A male subject aged around 60. A skin lesion imaged with a dermatoscope — 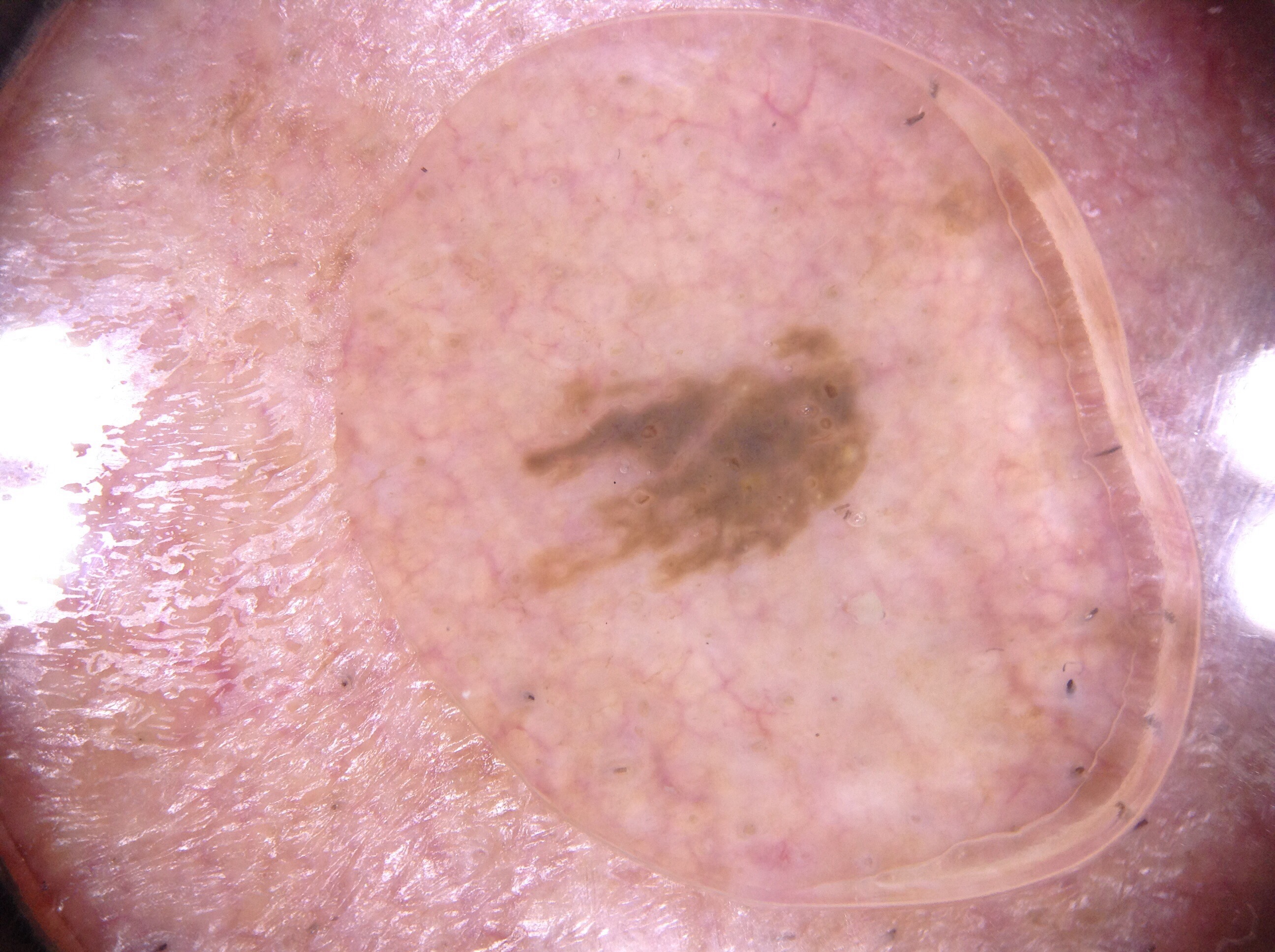dermoscopic_features:
  present:
    - milia-like cysts
  absent:
    - negative network
    - pigment network
    - streaks
lesion_location:
  bbox_xyxy:
    - 492
    - 281
    - 933
    - 619
diagnosis:
  name: seborrheic keratosis
  malignancy: benign
  lineage: keratinocytic
  provenance: clinical